Texture is reported as rough or flaky and raised or bumpy; the photo was captured at an angle; reported duration is one to four weeks; the patient described the issue as a rash; the affected area is the arm; Fitzpatrick skin type IV; the contributor notes darkening and itching.
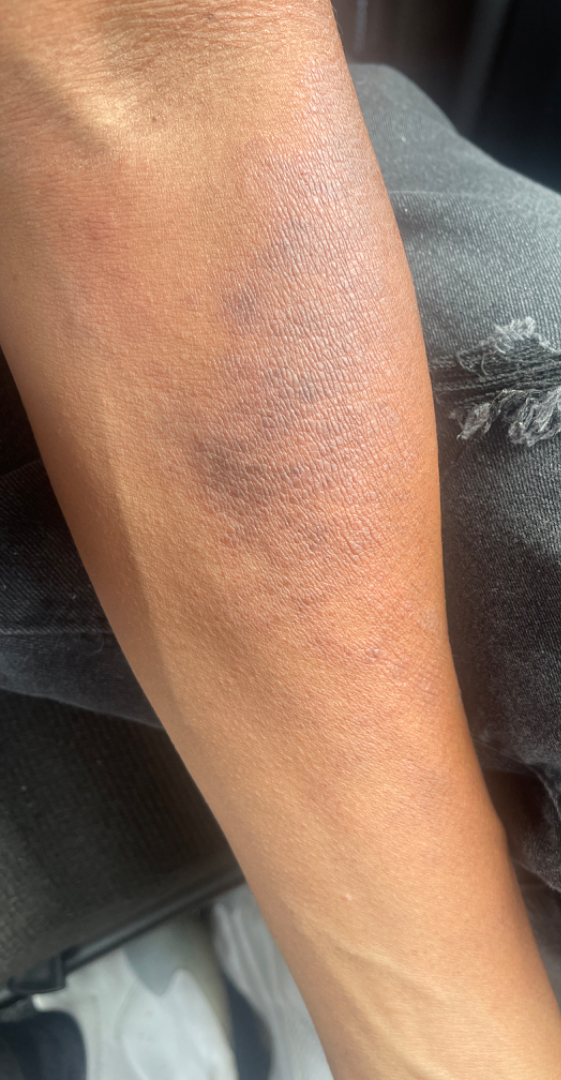Notes:
• assessment · indeterminate from the photograph